The chart documents a first-degree relative with melanoma but no prior melanoma. A dermoscopic close-up of a skin lesion — 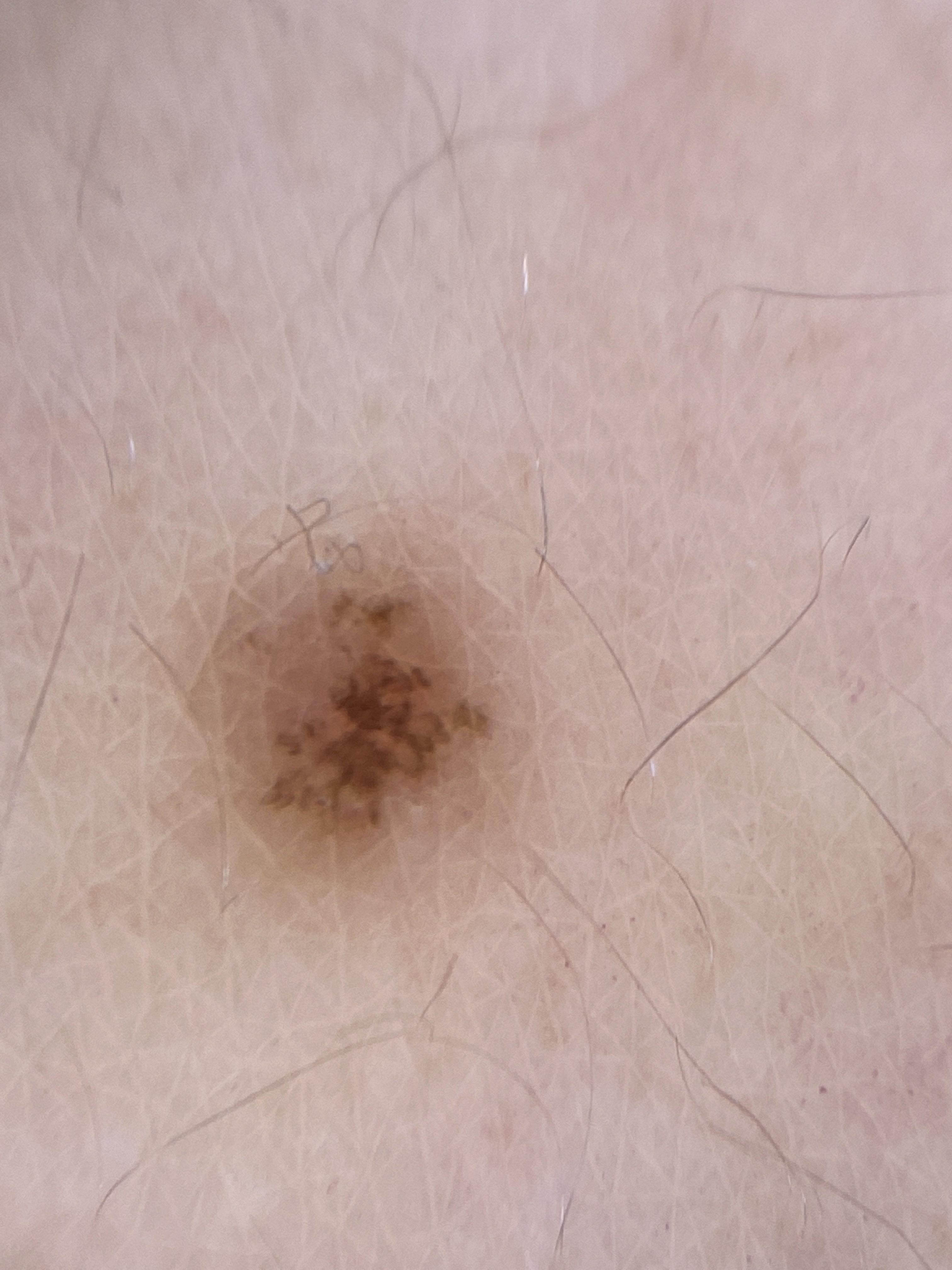| key | value |
|---|---|
| site | a lower extremity |
| diagnosis | Nevus (biopsy-proven) |